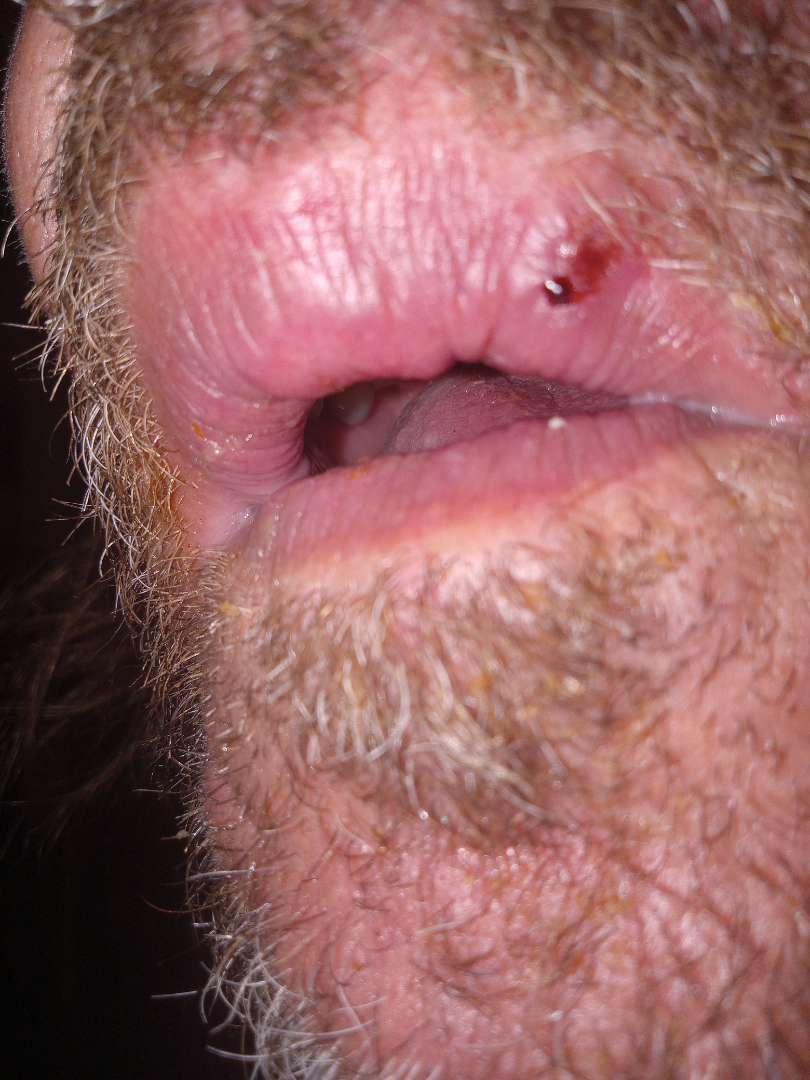The reviewing dermatologist was unable to assign a differential diagnosis from the image.